The front of the torso, back of the torso and arm are involved; a close-up photograph; male subject, age 18–29:
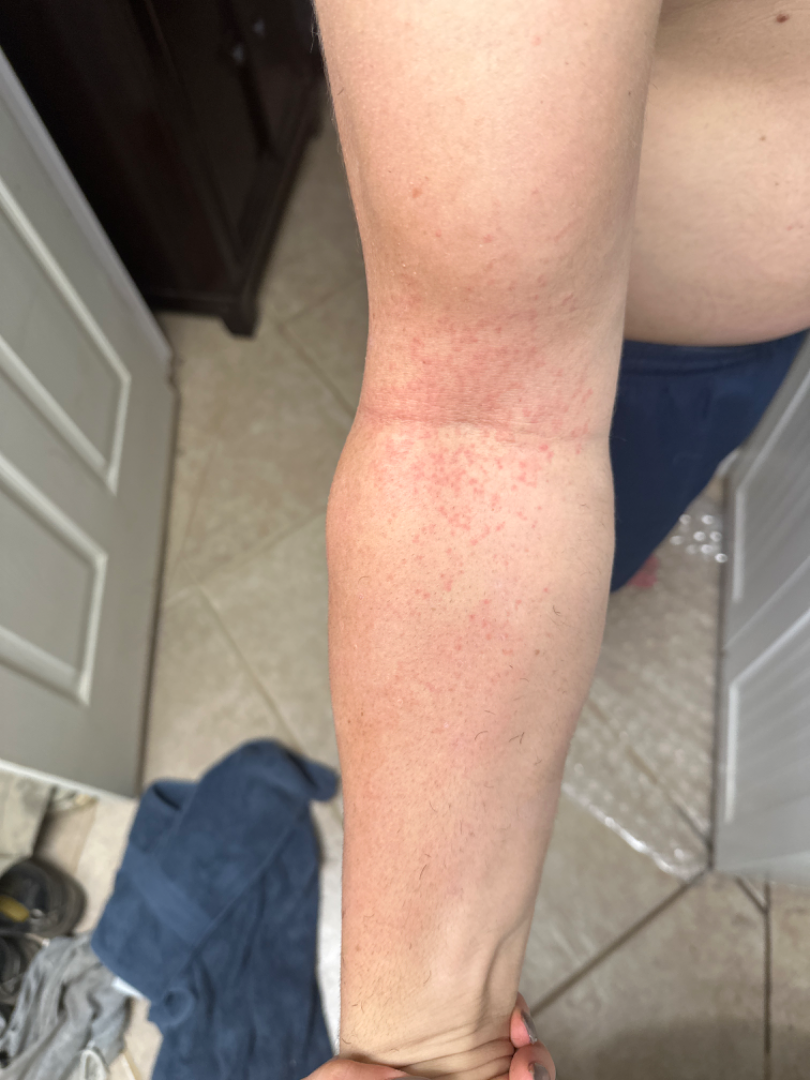  differential:
    tied_lead:
      - Eczema
      - Hypersensitivity
      - Allergic Contact Dermatitis